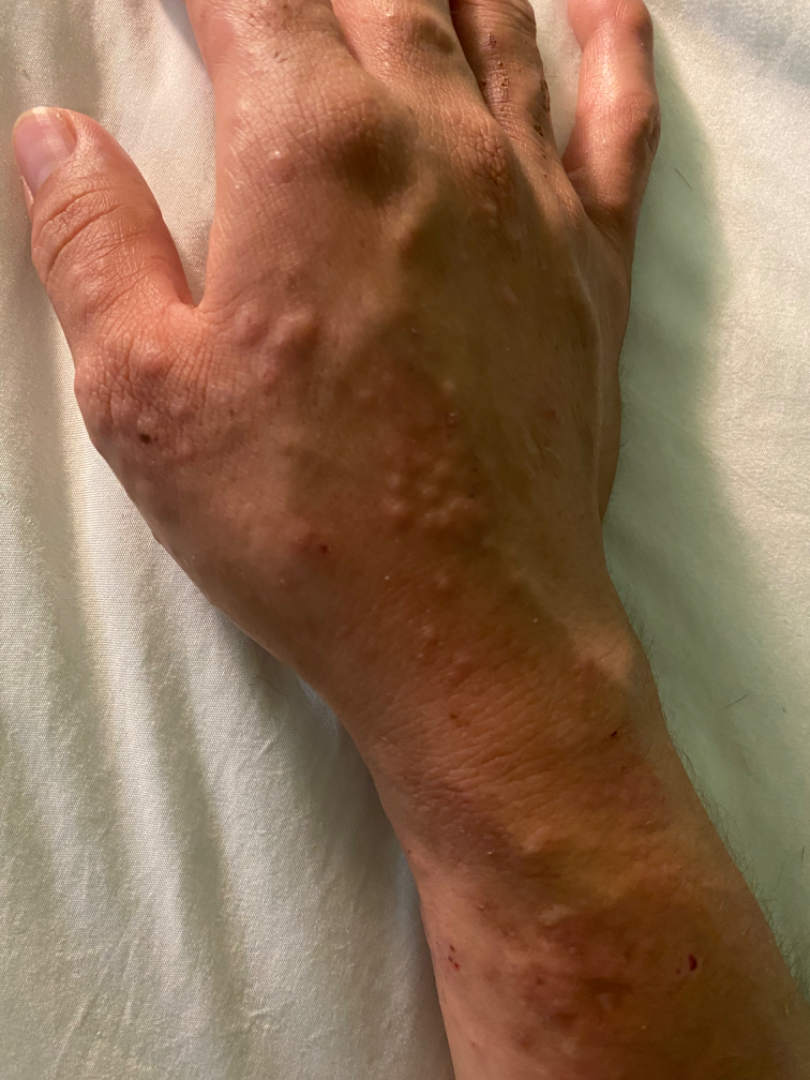Review:
The skin findings could not be characterized from the image.